Located on the arm. The photograph is a close-up of the affected area. The patient is 40–49, female:
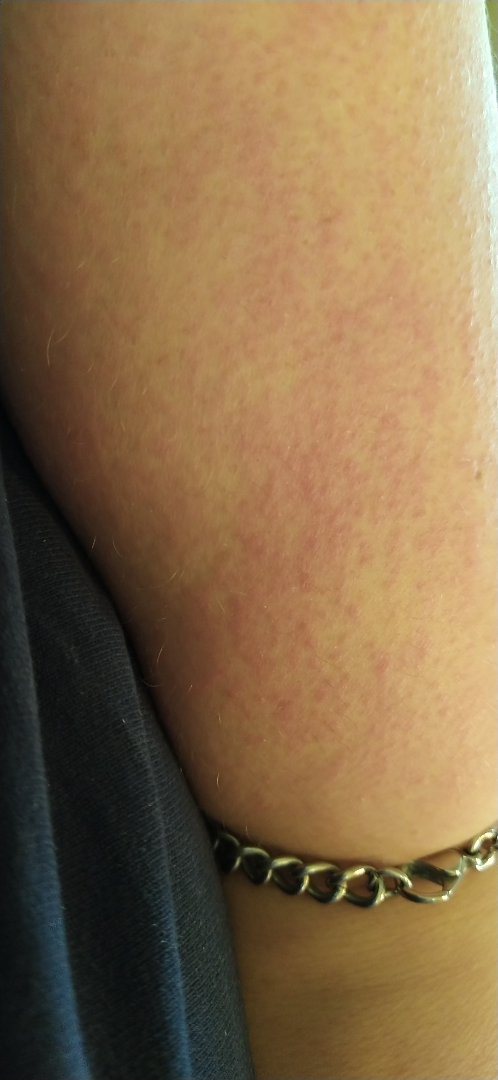  differential:
    leading:
      - Eczema
    considered:
      - Acute dermatitis, NOS
    unlikely:
      - Allergic Contact Dermatitis
      - Viral Exanthem
      - Keratosis pilaris